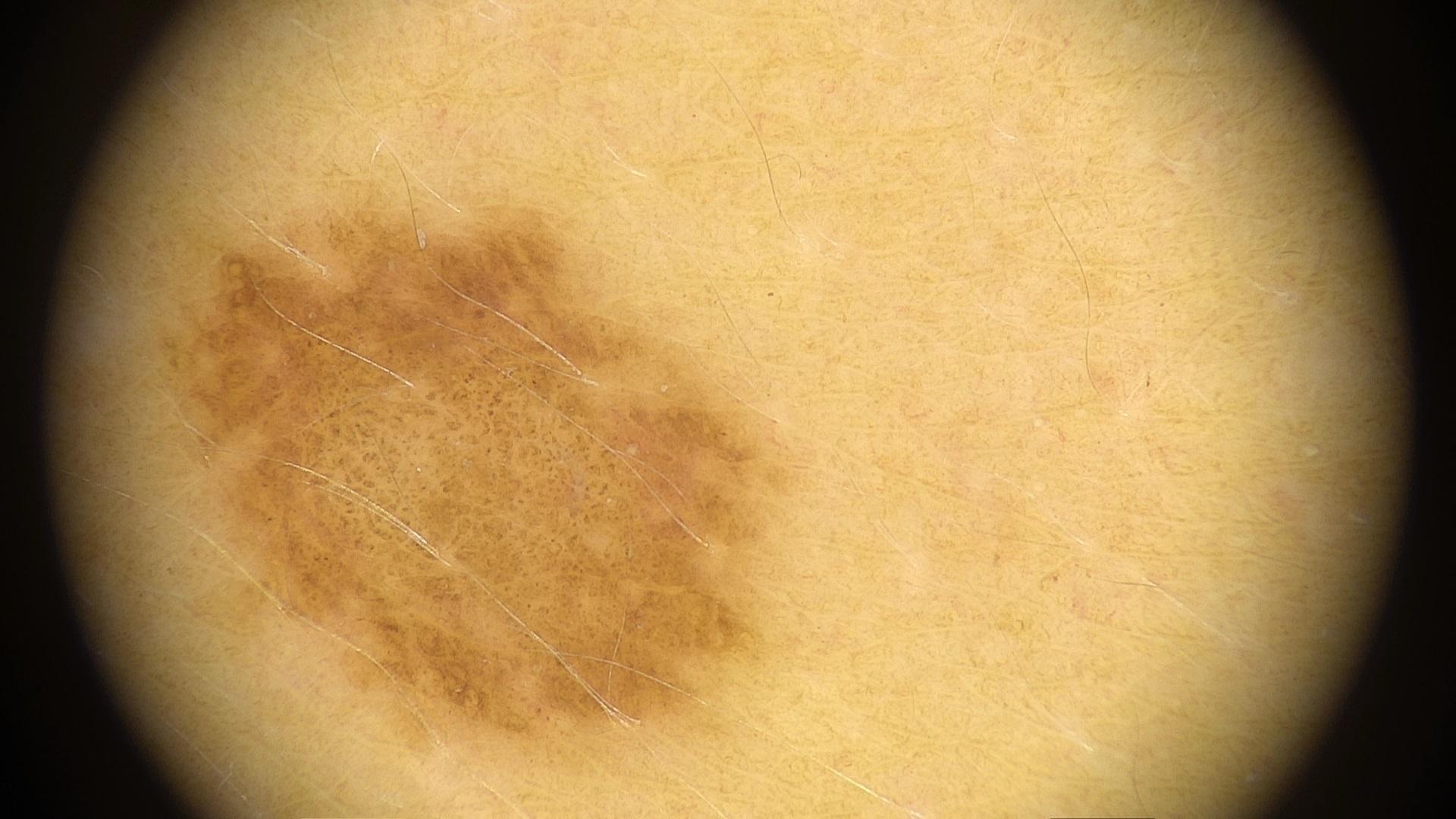The lesion was found on the trunk.
The clinical assessment was a nevus.